A clinical close-up photograph of a skin lesion · a subject aged 51: 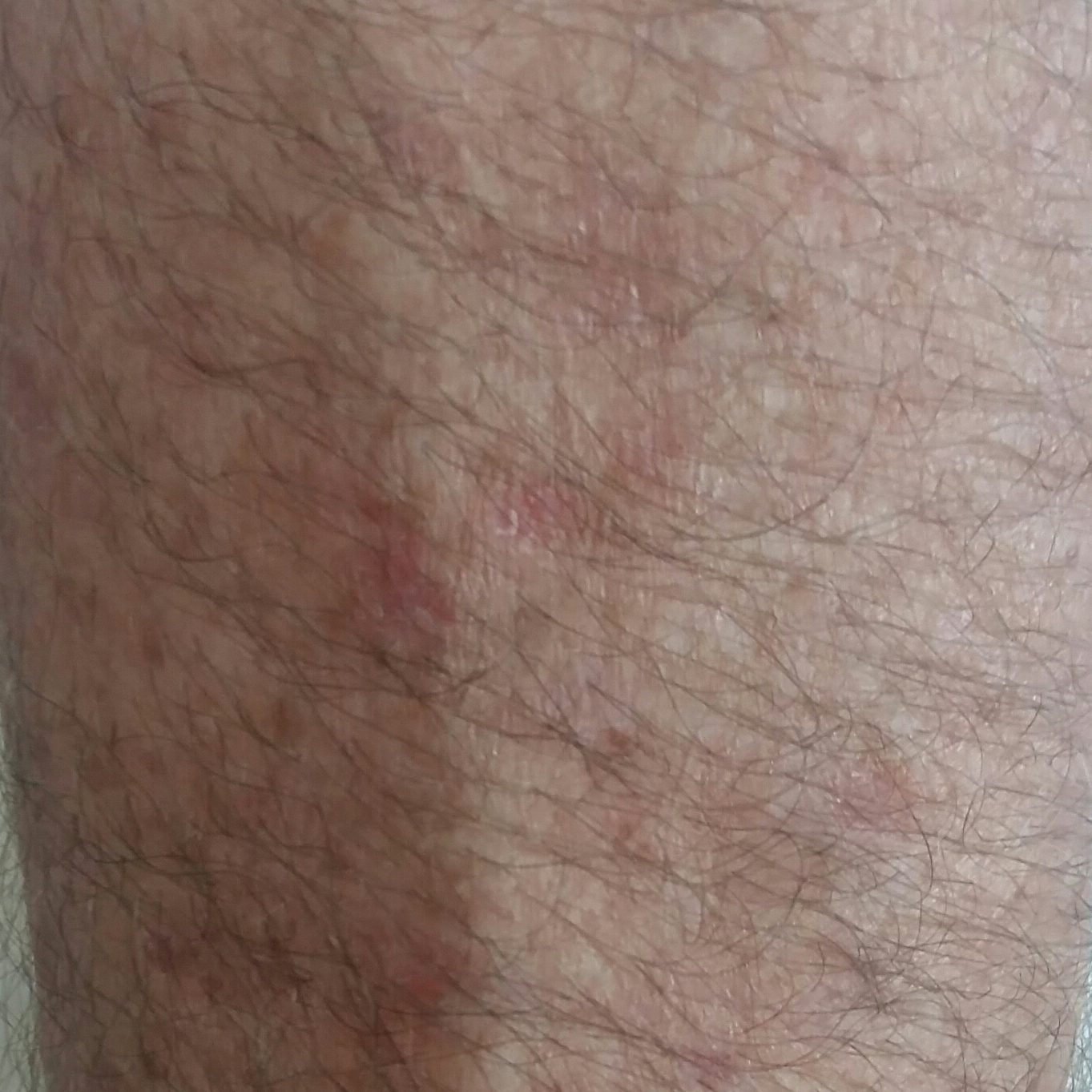Case summary: Per patient report, the lesion itches. Conclusion: Expert review favored an actinic keratosis.